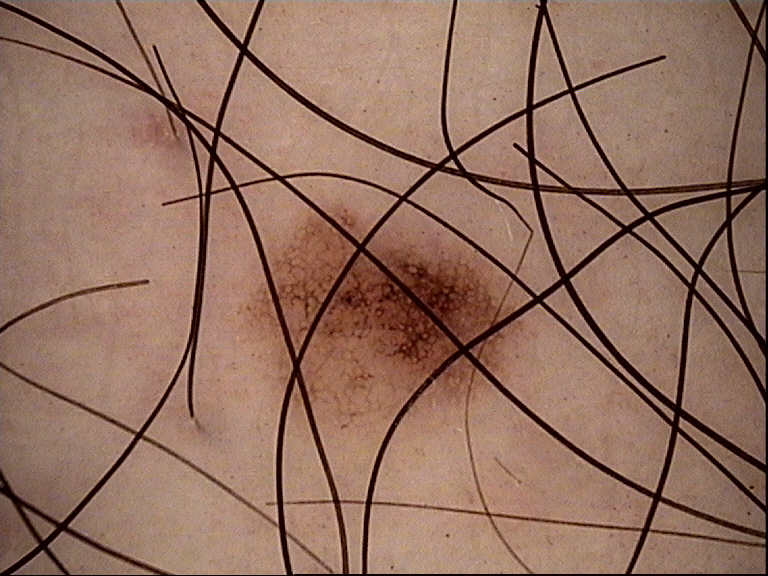modality = dermatoscopy, diagnosis = dysplastic junctional nevus (expert consensus).